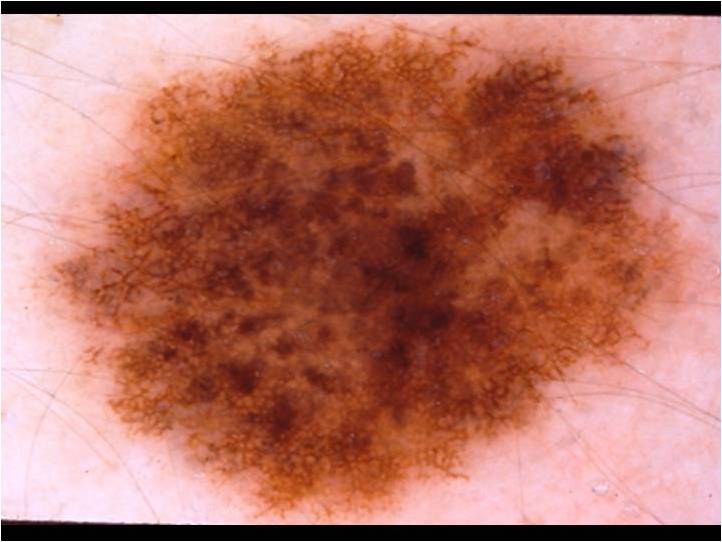Dermoscopy of a skin lesion. The patient is a female in their mid-20s. Dermoscopic review identifies pigment network. The lesion extends across almost the whole field of view. The diagnostic assessment was a melanocytic nevus.